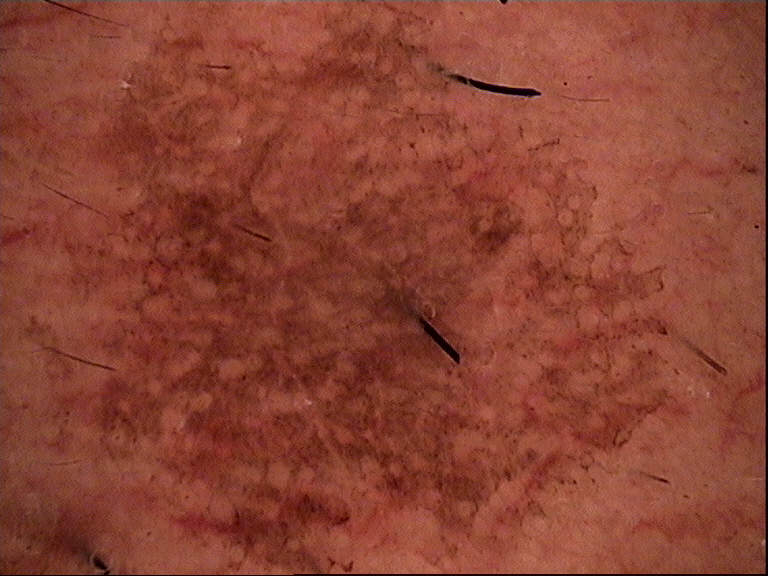A skin lesion imaged with a dermatoscope.
Labeled as a solar lentigo.